Recorded as skin type II; a female subject aged approximately 30: 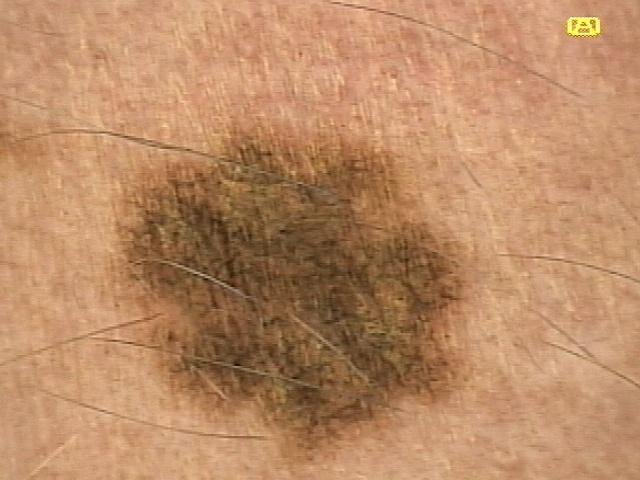The lesion is located on the trunk. Expert review favored a nevus.